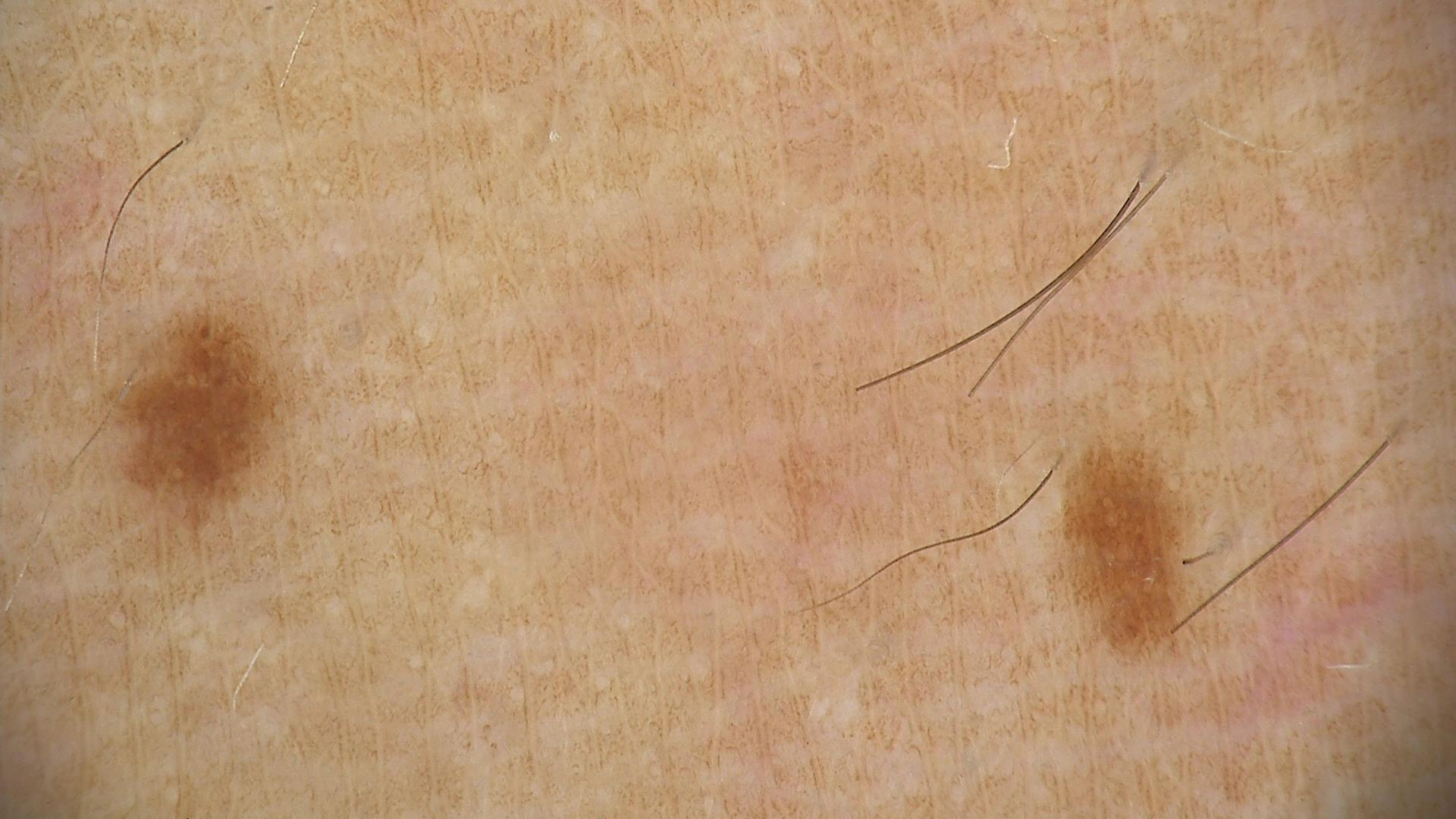The diagnostic label was a dysplastic junctional nevus.